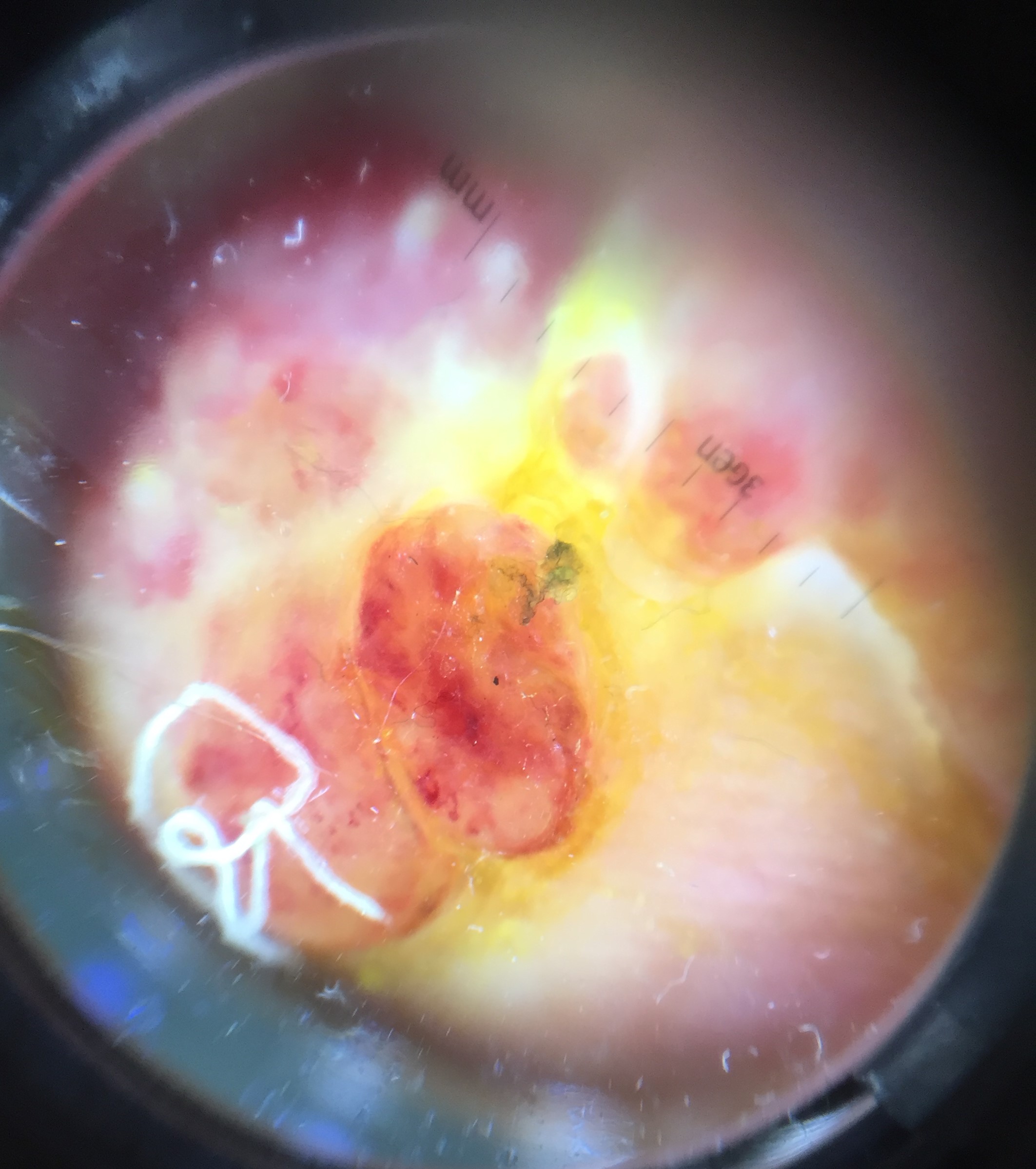pathology — acral nodular melanoma (biopsy-proven).